A dermoscopic photograph of a skin lesion.
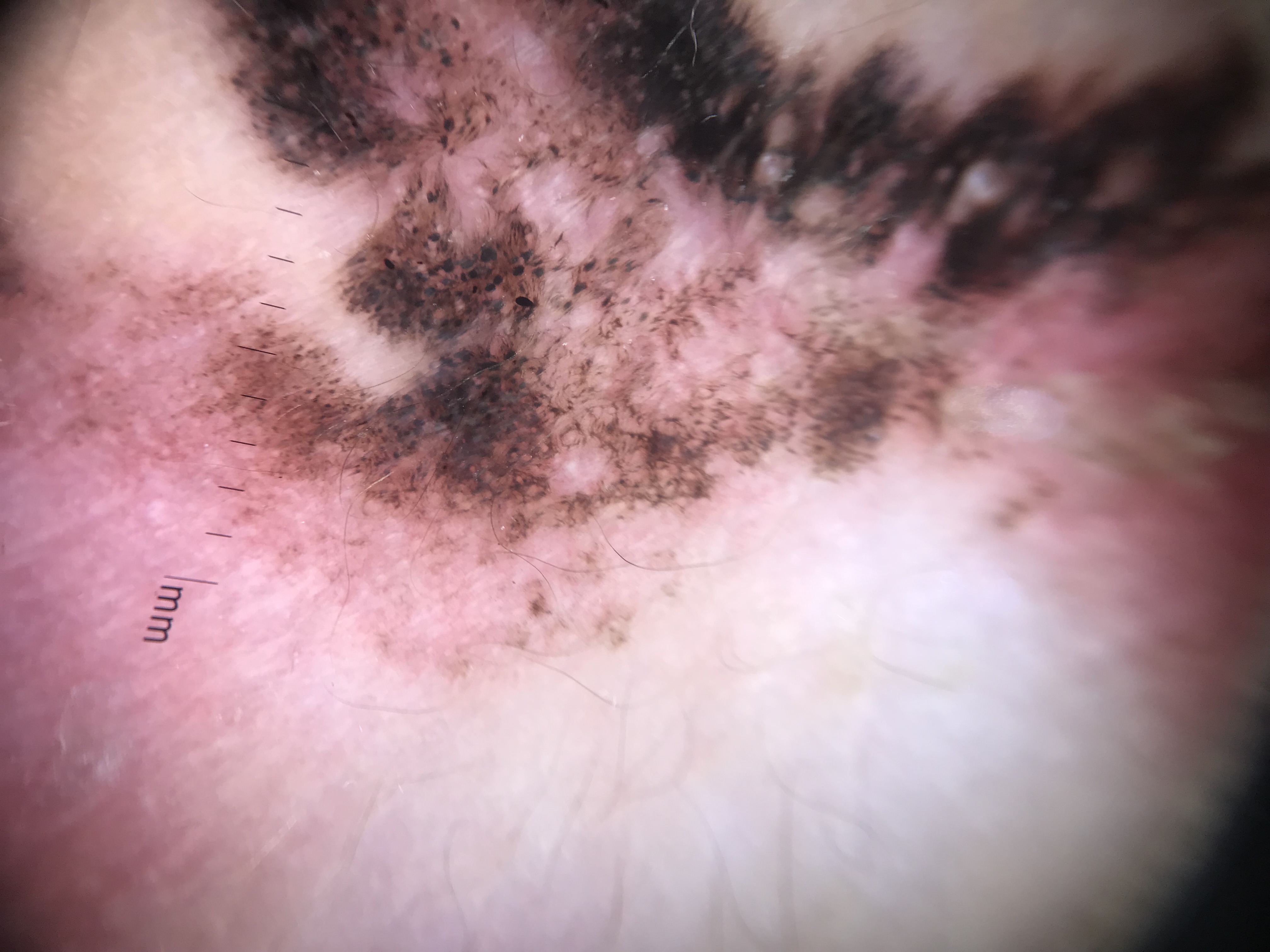Conclusion:
Histopathology confirmed a melanoma.